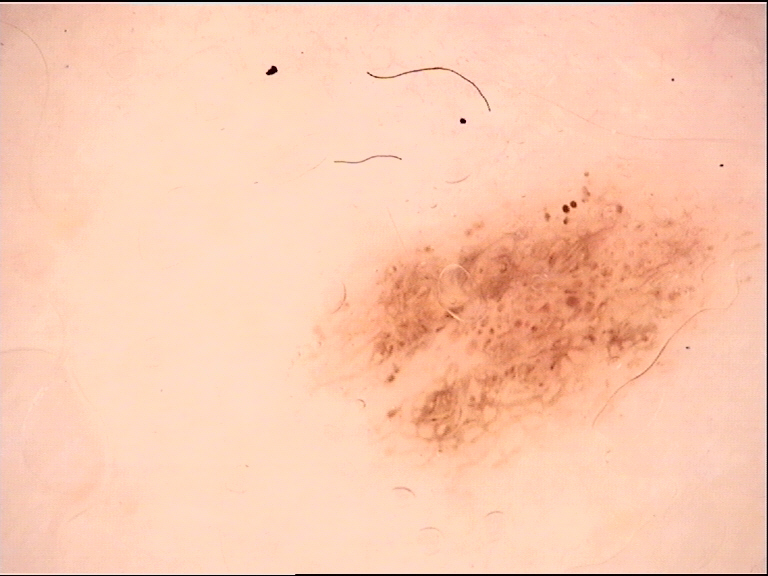Findings:
Dermoscopy of a skin lesion.
Conclusion:
Classified as a dysplastic junctional nevus.